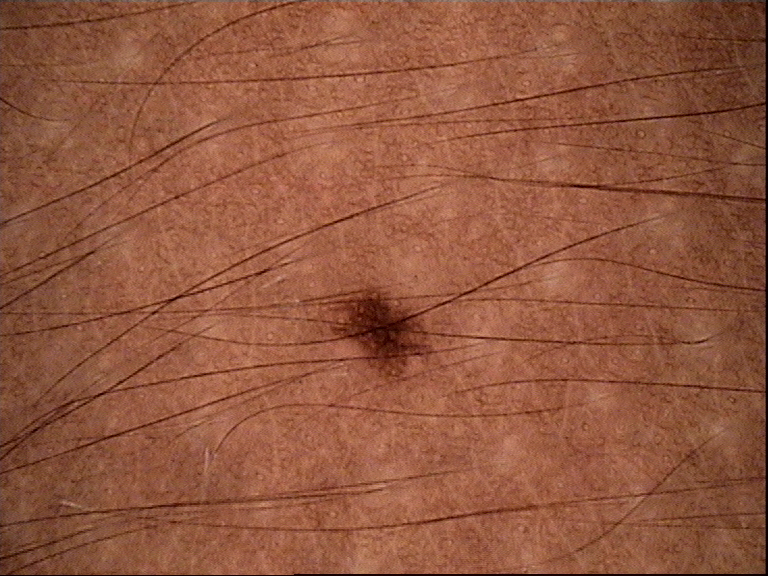image: dermatoscopy; assessment: junctional nevus (expert consensus).